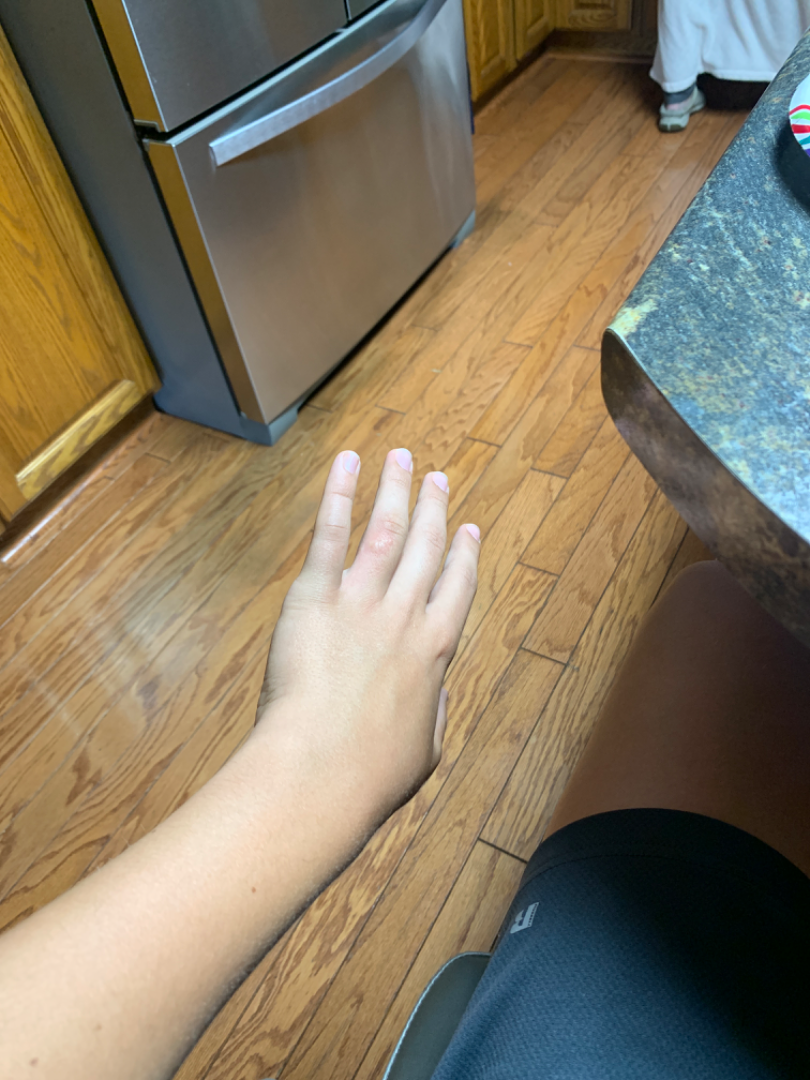Review:
The case was difficult to assess from the available photograph.
Patient information:
This image was taken at a distance. Male patient, age 18–29. Reported lesion symptoms include itching, pain and enlargement. The patient also reports mouth sores. The lesion is described as fluid-filled.